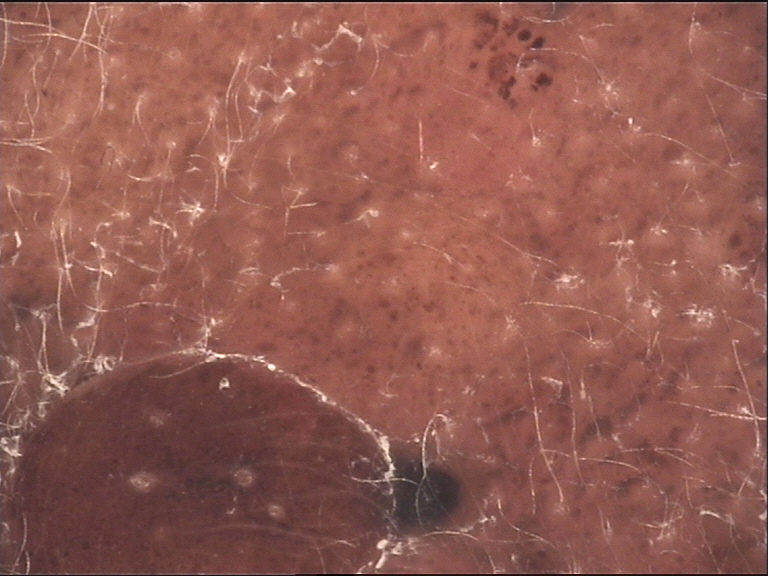Findings:
- diagnostic label — congenital compound nevus (expert consensus)